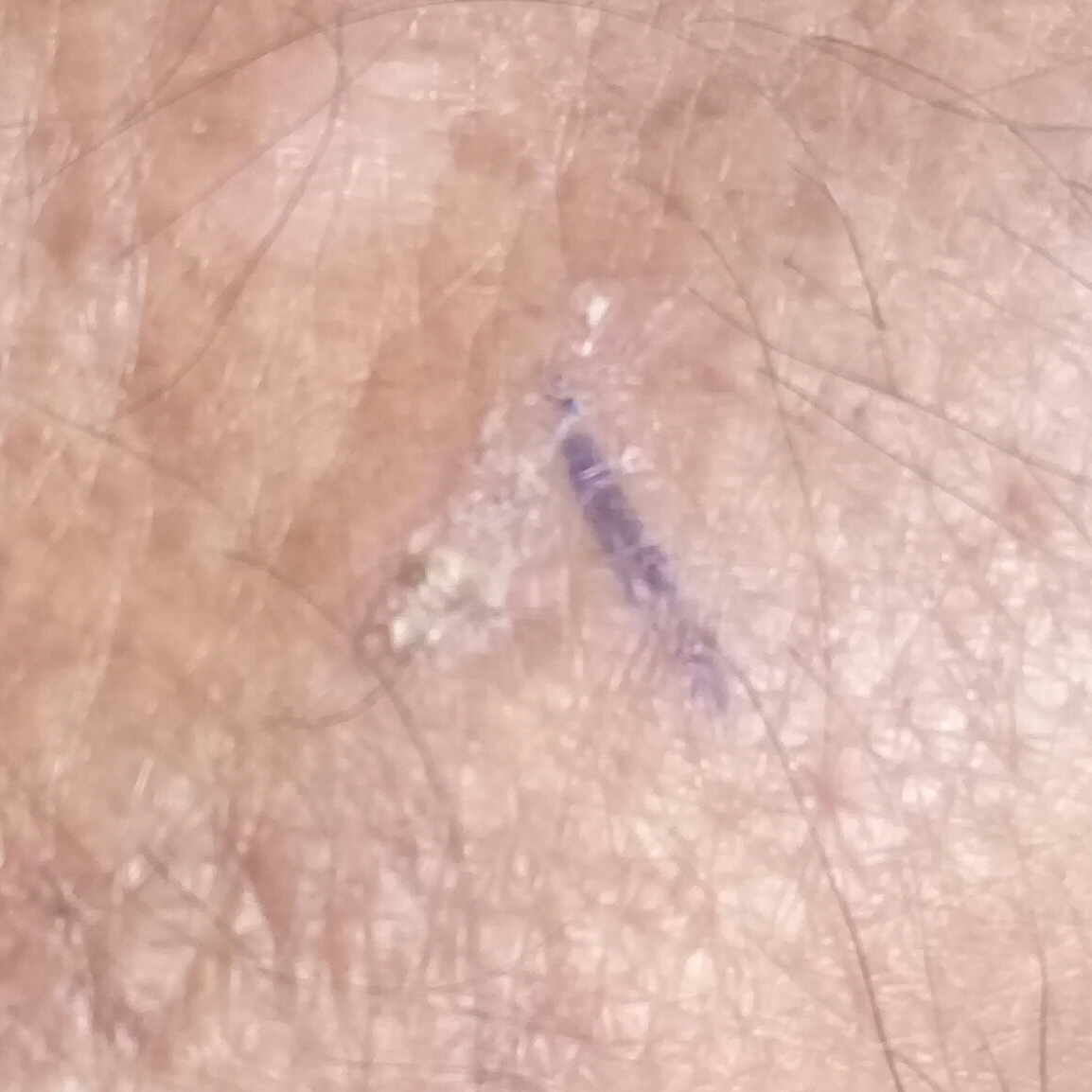Findings: A patient age 81. A smartphone photograph of a skin lesion. The lesion is on a forearm. The patient reports that the lesion does not itch and is not elevated. Conclusion: Consistent with an actinic keratosis.